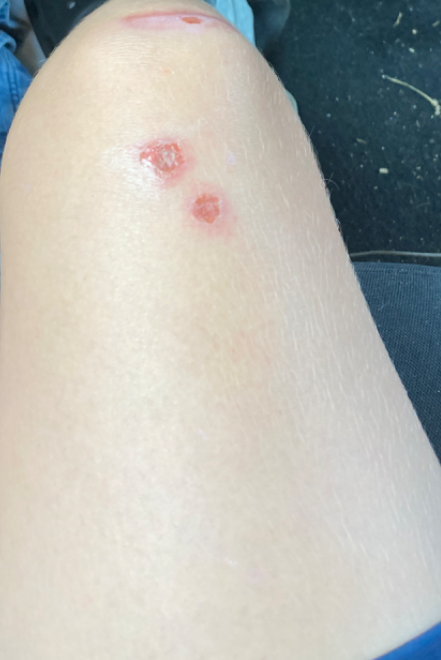The photograph was taken at a distance. On dermatologist assessment of the image: Ecthyma (weight 0.50); Impetigo (weight 0.50).